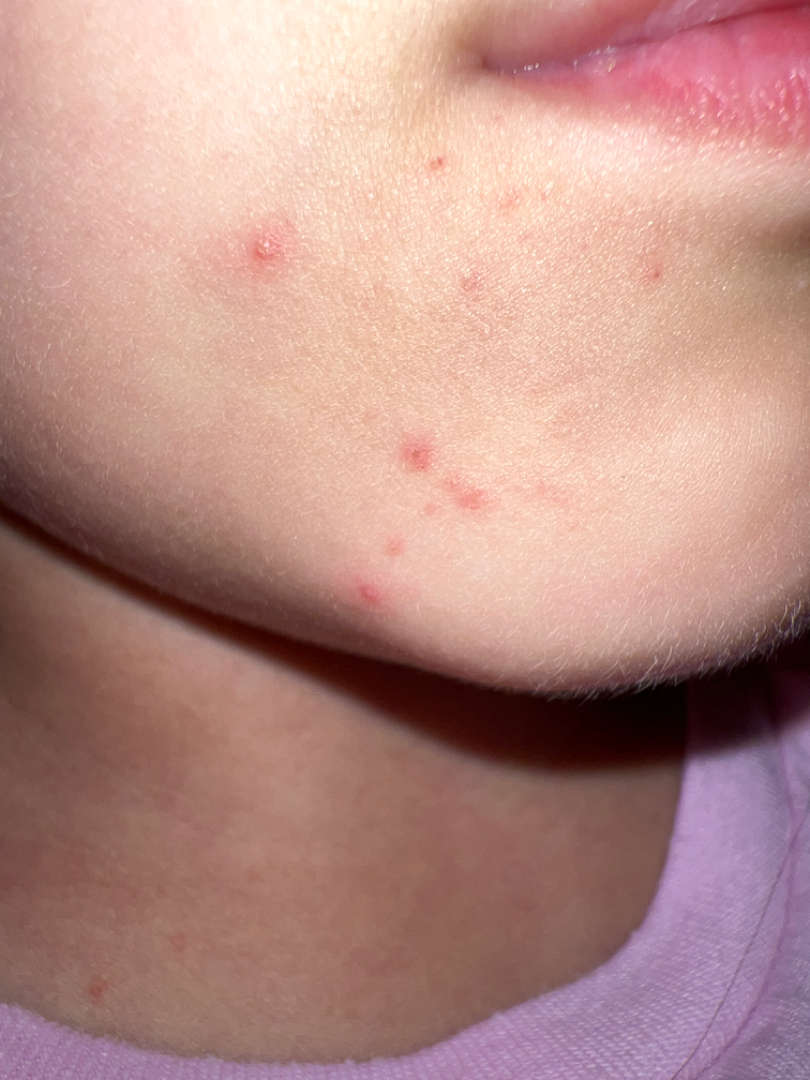image framing: at an angle, skin tone: human graders estimated MST 2–3, impression: favoring Acne.